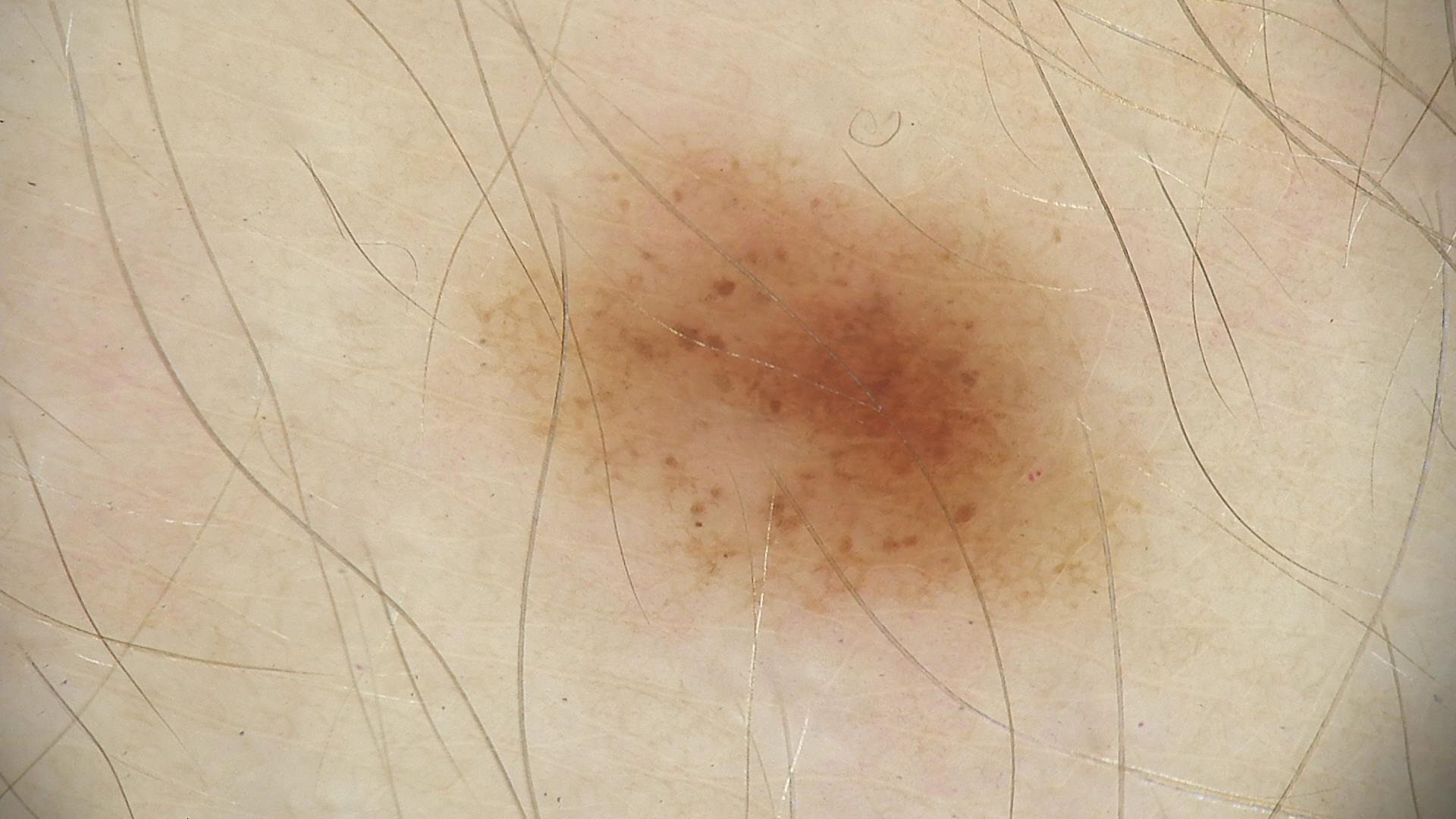diagnosis: dysplastic junctional nevus (expert consensus)